A dermoscopic photograph of a skin lesion: 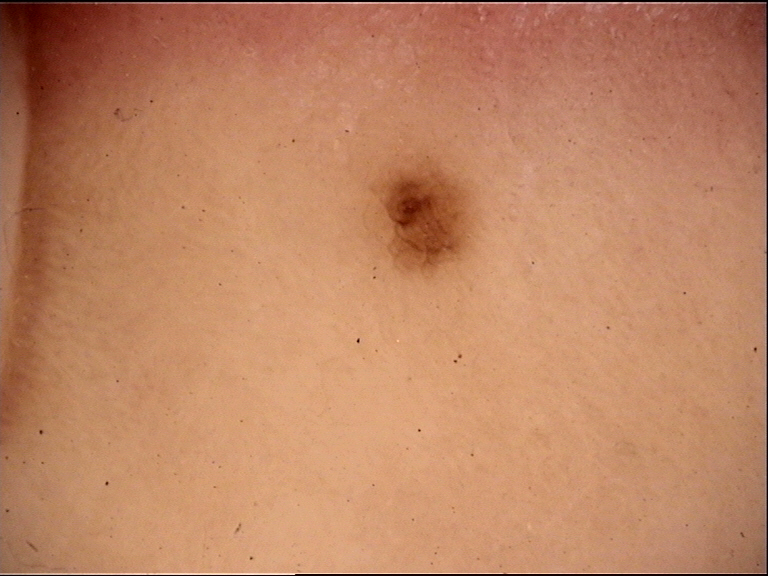The diagnosis was a dysplastic compound nevus.